A skin lesion imaged with a dermatoscope; a male patient, roughly 25 years of age — 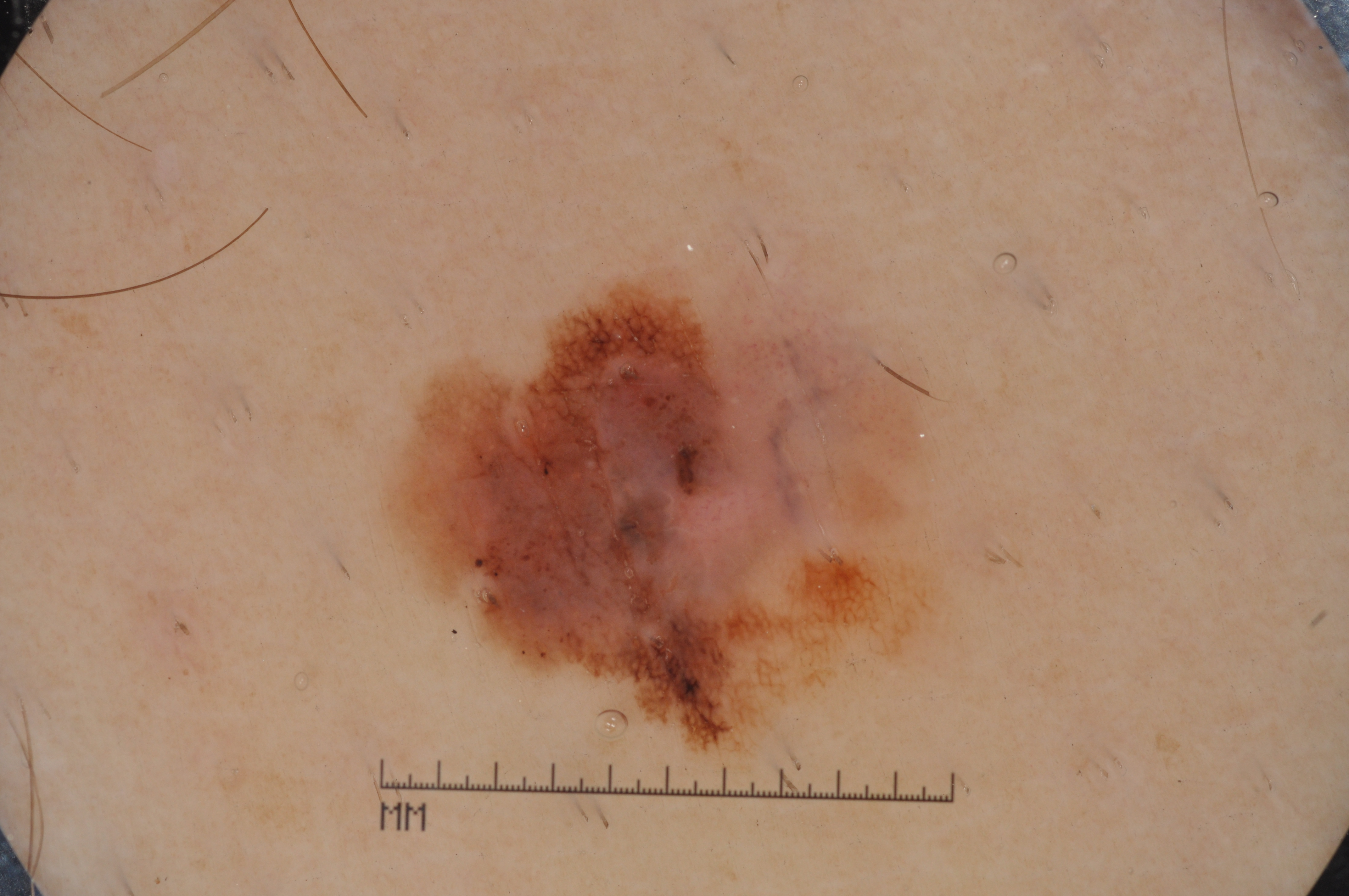dermoscopic_features:
  present:
    - milia-like cysts
    - negative network
    - pigment network
  absent:
    - streaks
lesion_extent:
  approx_field_fraction_pct: 21
lesion_location:
  bbox_xyxy:
    - 367
    - 205
    - 982
    - 777
diagnosis:
  name: melanoma
  malignancy: malignant
  lineage: melanocytic
  provenance: histopathology